The front of the torso is involved. The photo was captured at a distance:
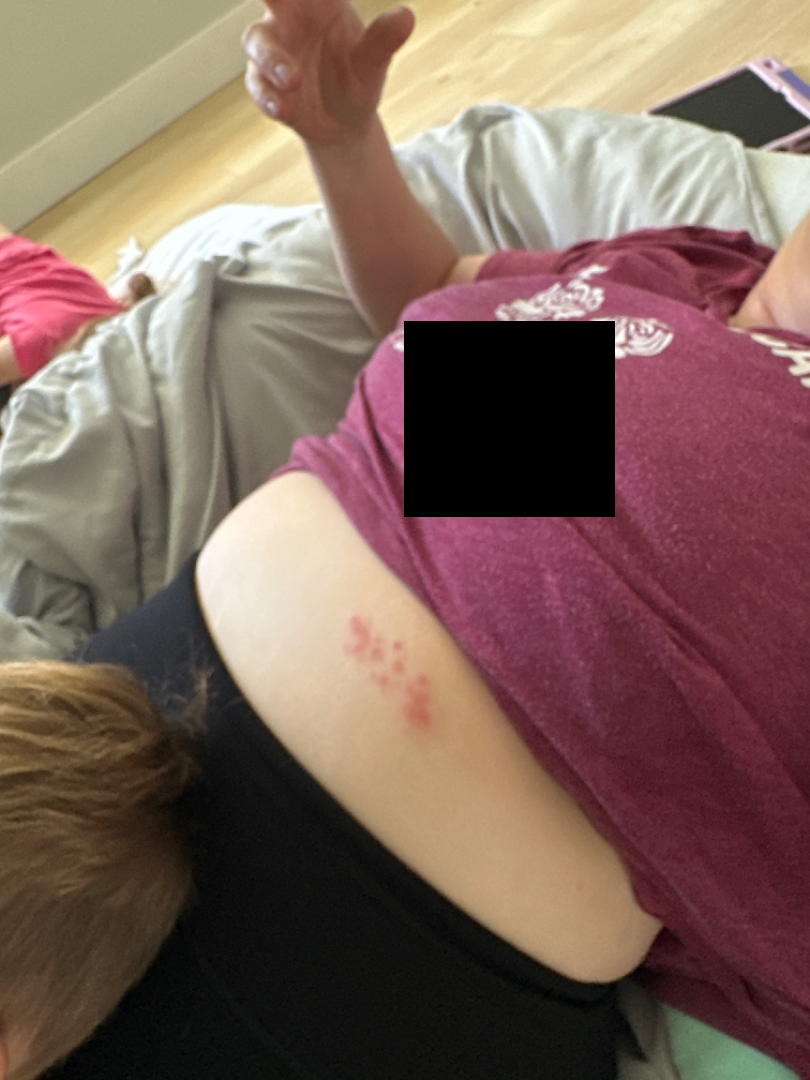On remote dermatologist review, Herpes Simplex (0.55); Herpes Zoster (0.27); Skin and soft tissue atypical mycobacterial infection (0.18).